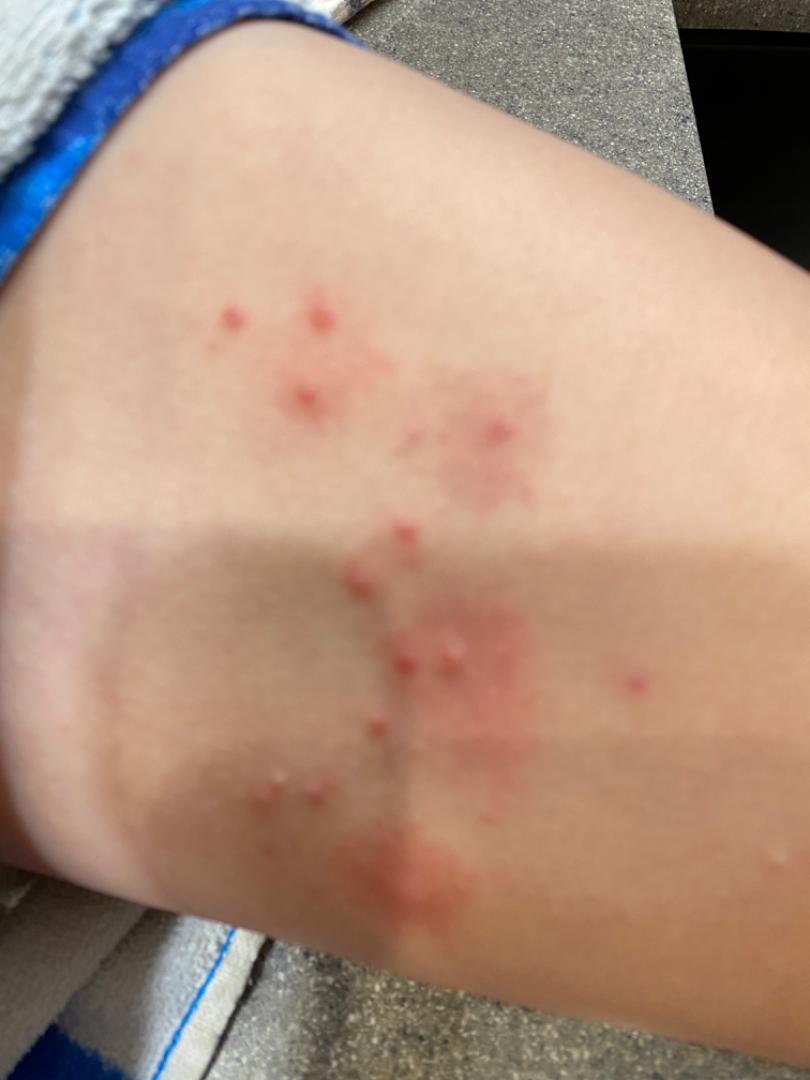{
  "symptoms": [
    "bothersome appearance",
    "itching"
  ],
  "duration": "one to three months",
  "patient_category": "a rash",
  "systemic_symptoms": "none reported",
  "texture": "raised or bumpy",
  "shot_type": "close-up",
  "body_site": "leg",
  "differential": {
    "leading": [
      "Molluscum Contagiosum"
    ]
  }
}